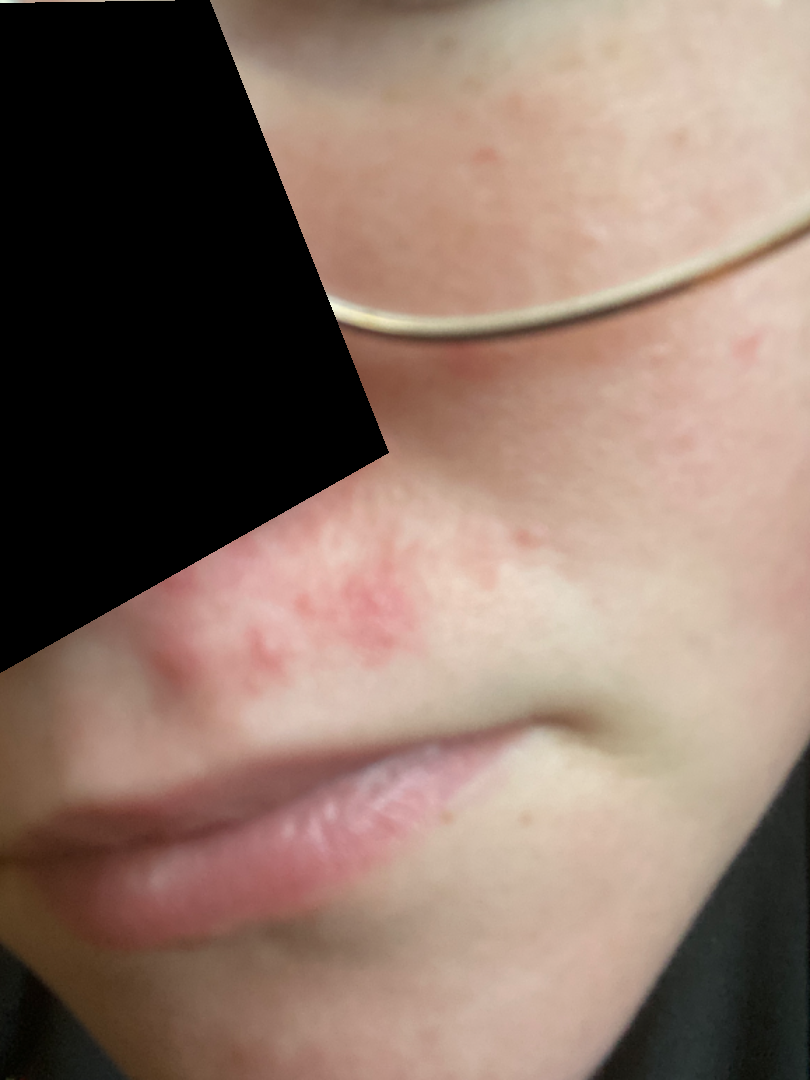This is a close-up image. The reviewing clinician's impression was: consistent with Perioral Dermatitis.